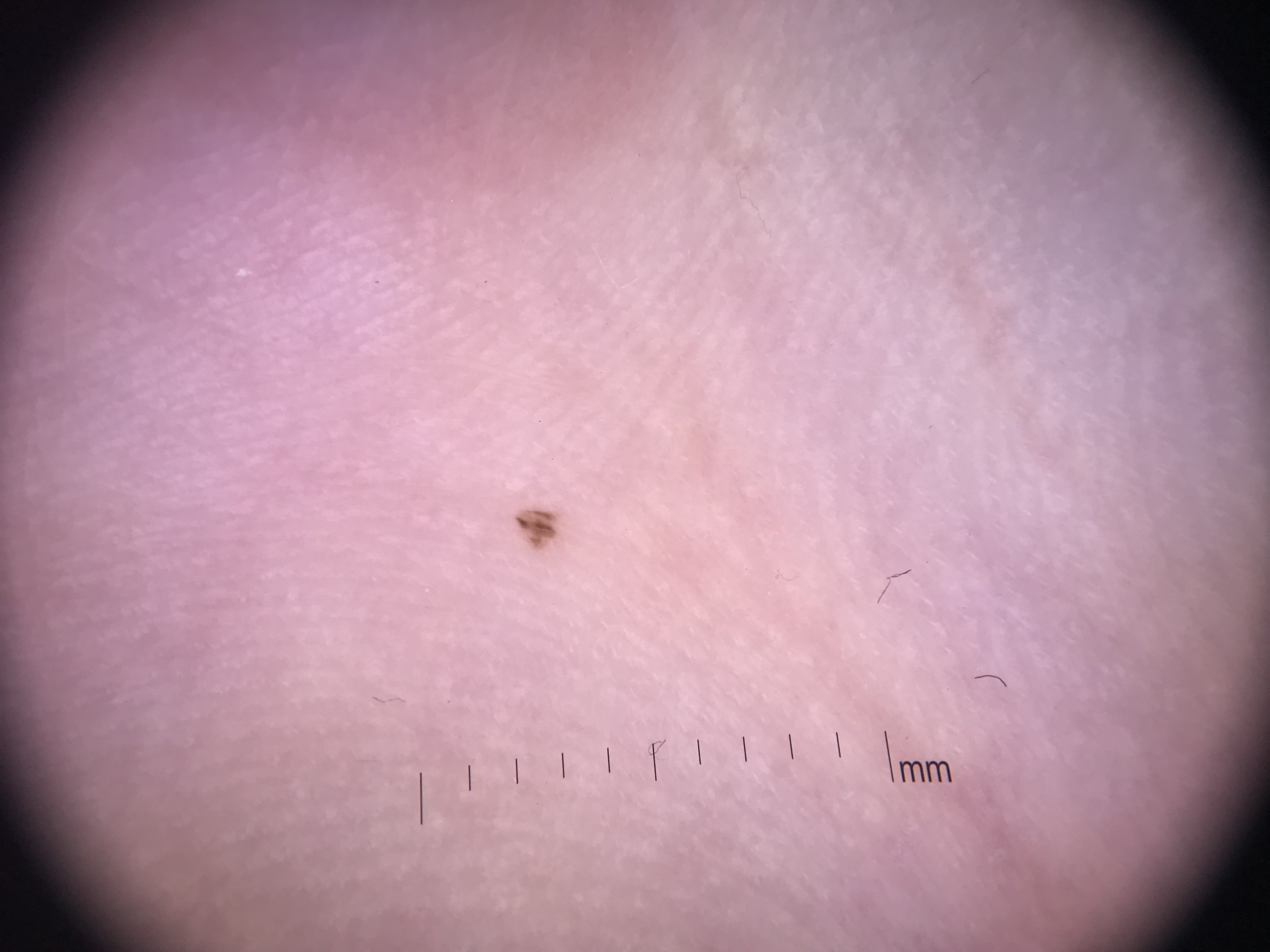assessment: acral junctional nevus (expert consensus)